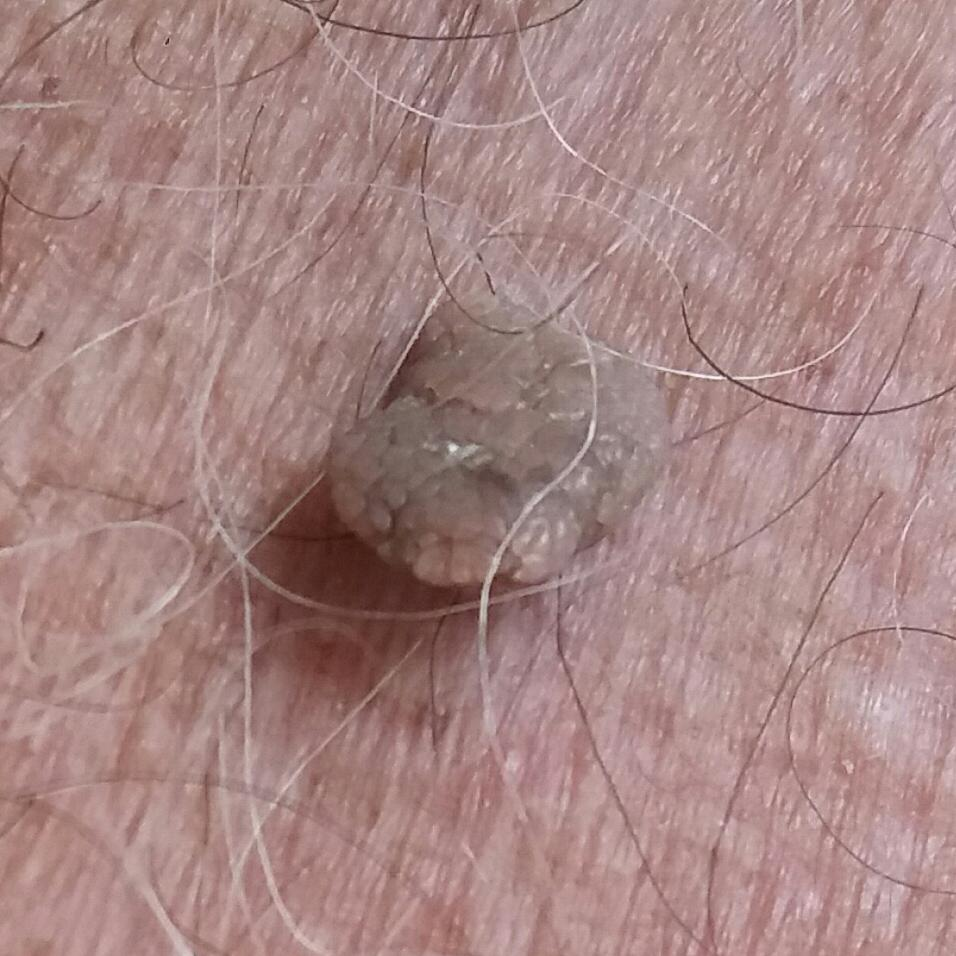A clinical photograph showing a skin lesion. A male patient 80 years of age. The lesion involves a forearm. Per patient report, the lesion is elevated and has grown. The clinical impression was a seborrheic keratosis.